Located on the leg; reported lesion symptoms include itching and bleeding; female contributor, age 18–29; the contributor notes the lesion is raised or bumpy and flat; present for one to four weeks; the patient considered this a rash; the photograph was taken at a distance; lay graders estimated 2 on the MST:
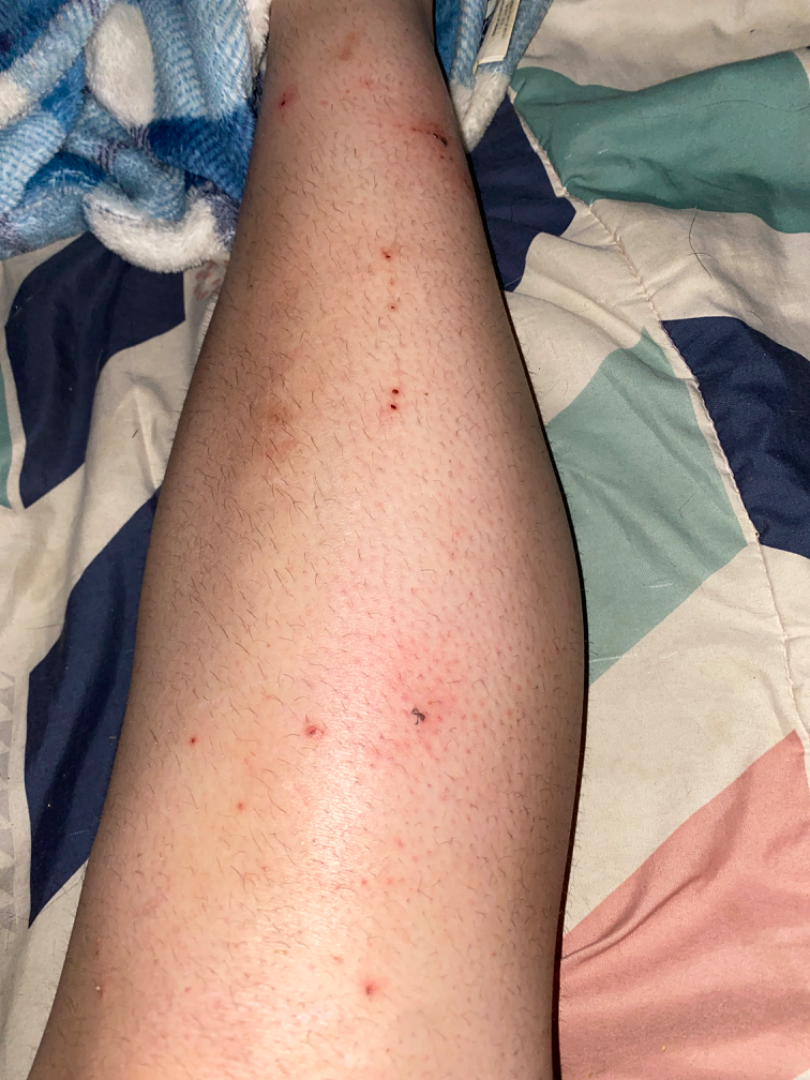Assessment: The primary impression is Folliculitis; lower on the differential is Acute dermatitis, NOS; less likely is Ingrown hair; less probable is Insect Bite; a remote consideration is Infection of tick bite; a more distant consideration is Eczema; lower on the differential is Hypersensitivity.